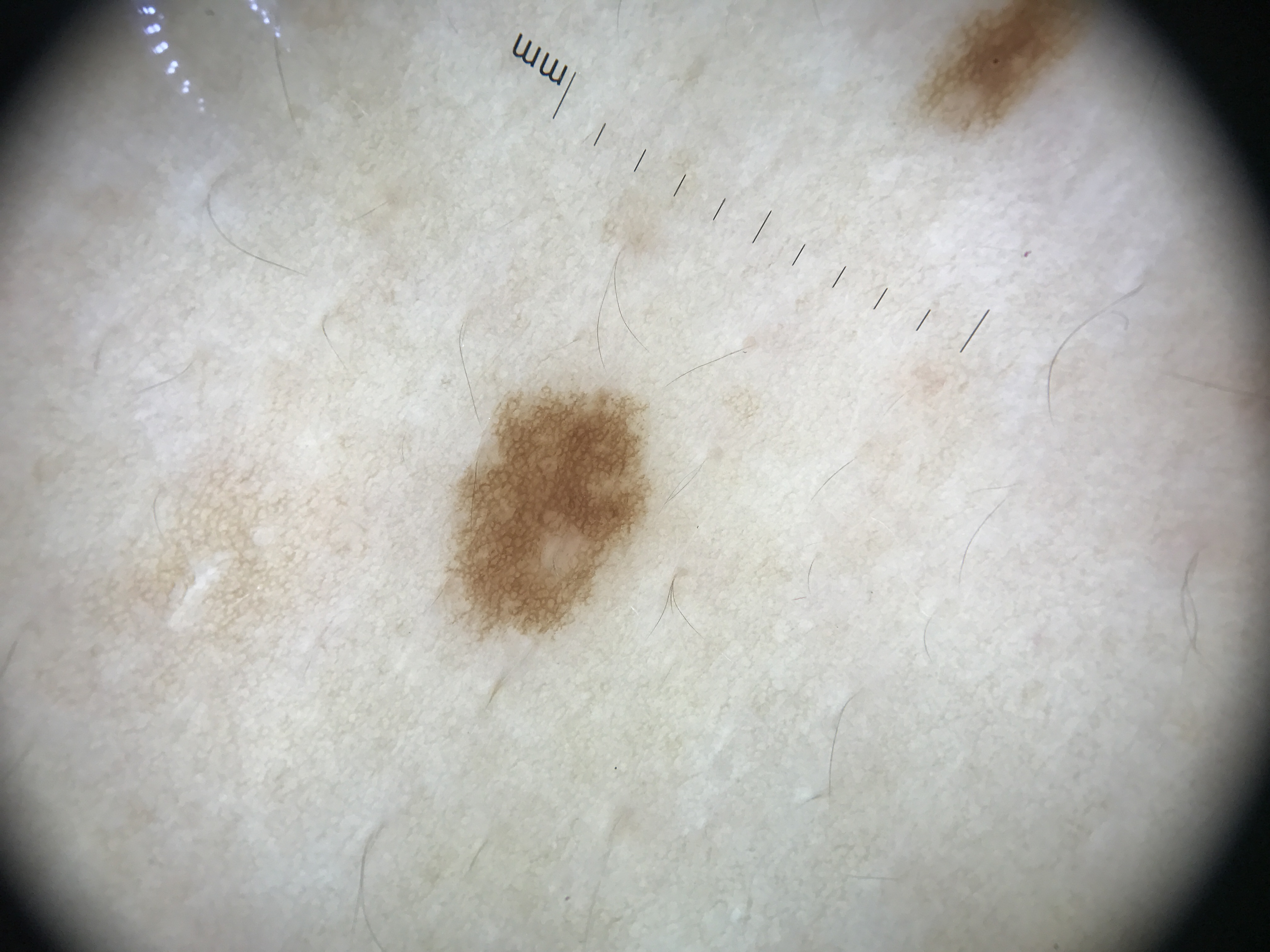image: dermoscopy; lesion type: banal; assessment: junctional nevus (expert consensus).